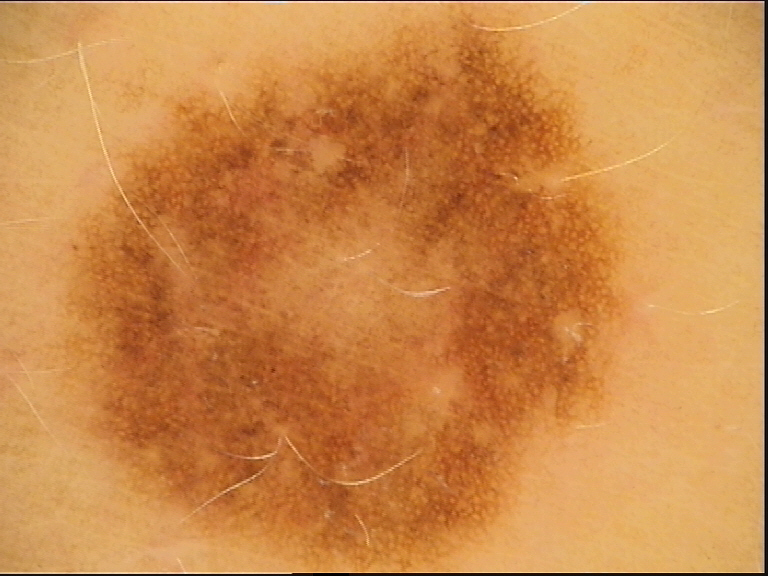A dermoscopy image of a single skin lesion. Consistent with a dysplastic junctional nevus.